Collected as part of a research study, without a referral diagnosis · a male patient 62 years old · a macroscopic clinical photograph of a skin lesion:
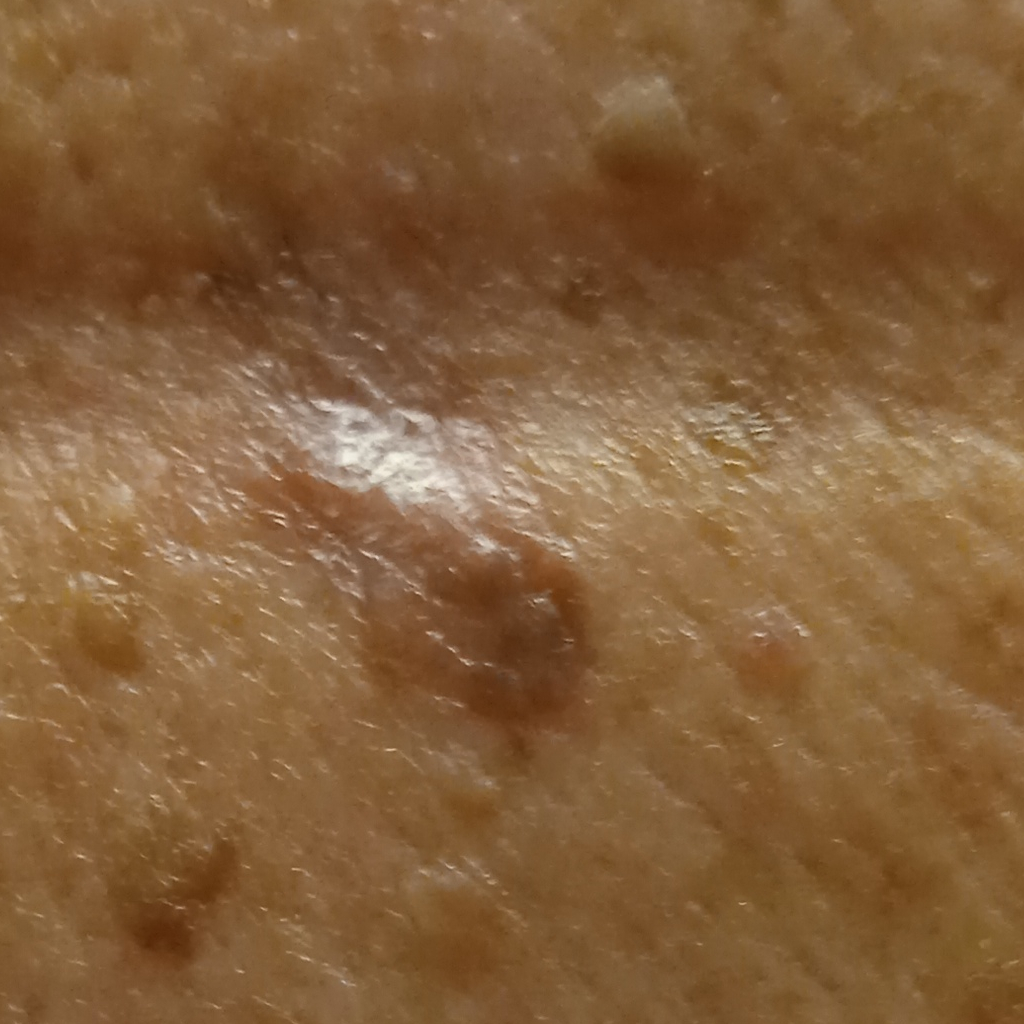Clinical context:
Located on the back. The lesion measures approximately 13.8 mm.
Impression:
The lesion was assessed as a squamous cell carcinoma.